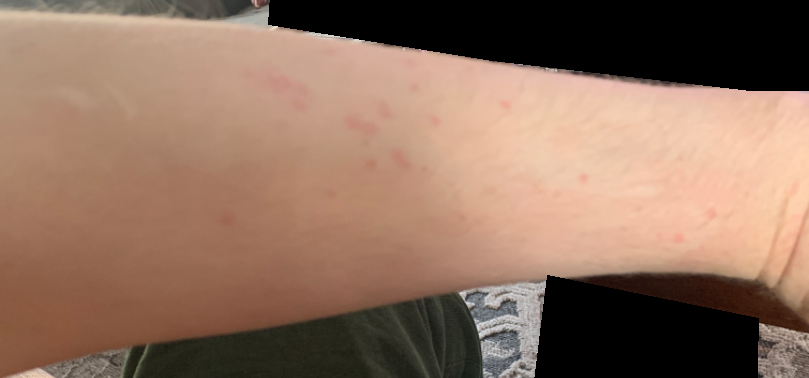The case was difficult to assess from the available photograph. The lesion is described as flat and raised or bumpy. Present for about one day. The patient described the issue as a rash. The contributor notes enlargement and itching. The lesion involves the leg, arm and head or neck. The photo was captured at a distance.